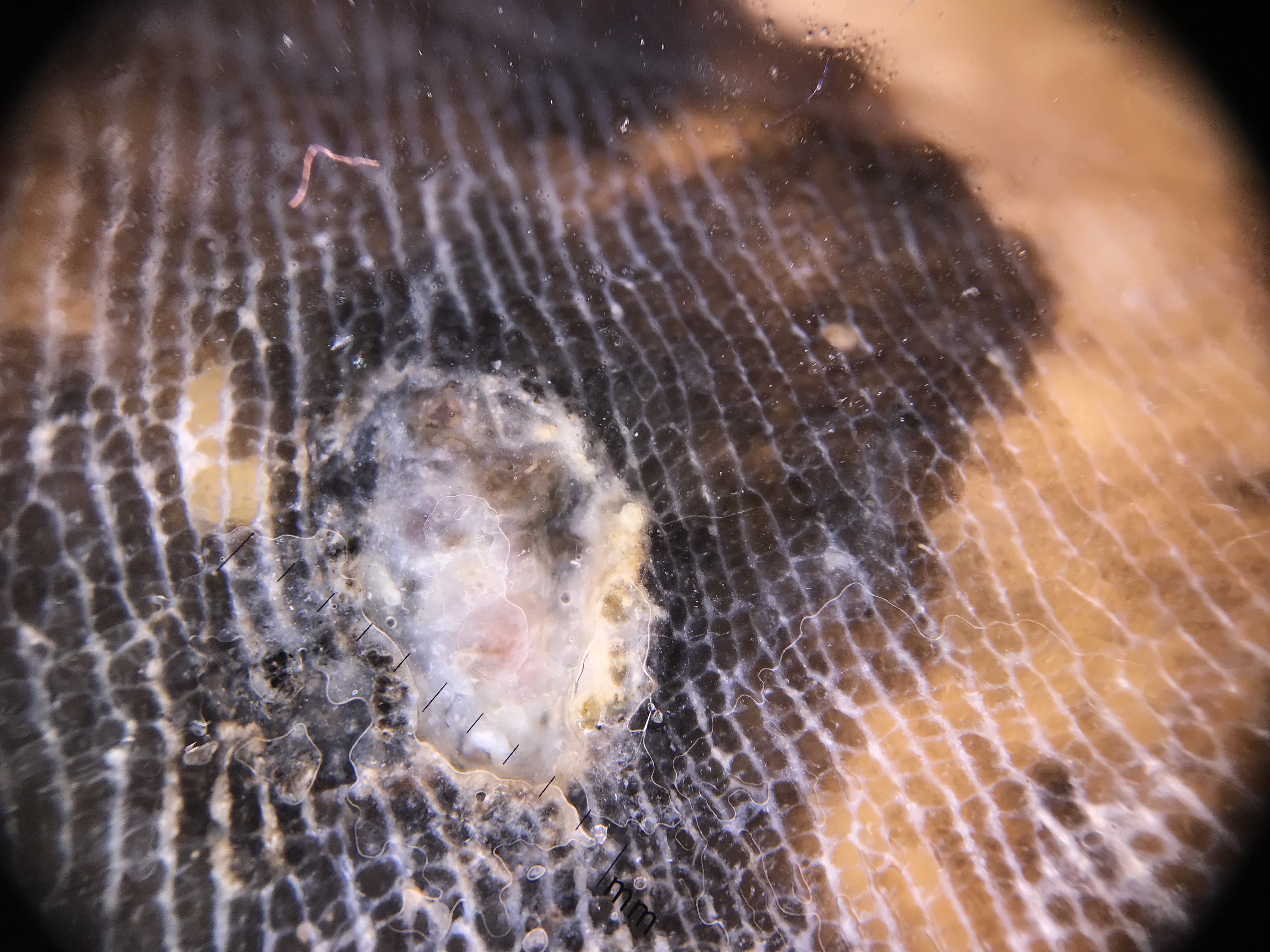imaging=dermoscopy | diagnosis=acral lentiginous melanoma (biopsy-proven).